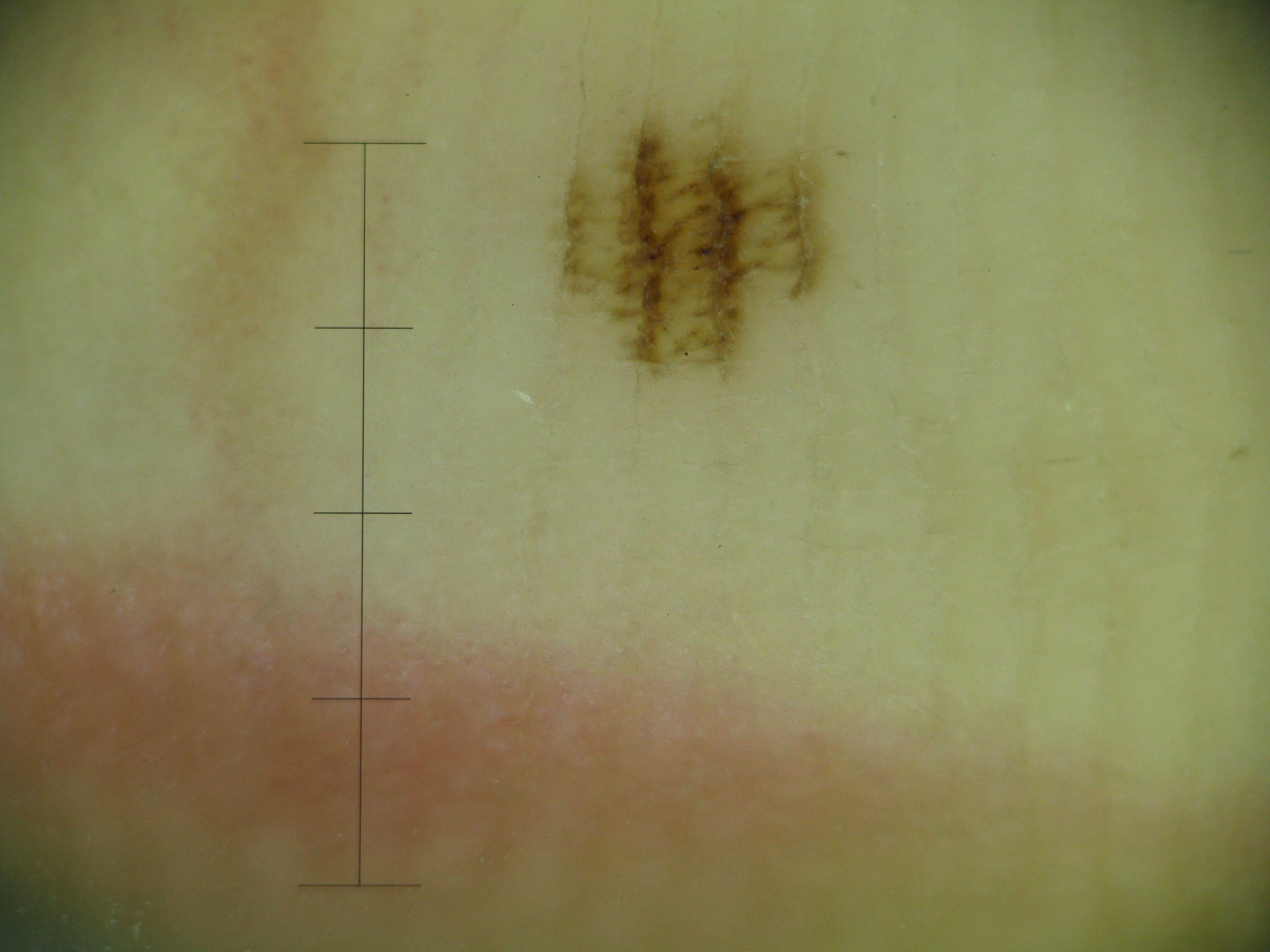image = dermoscopy | subtype = banal | diagnostic label = acral junctional nevus (expert consensus).